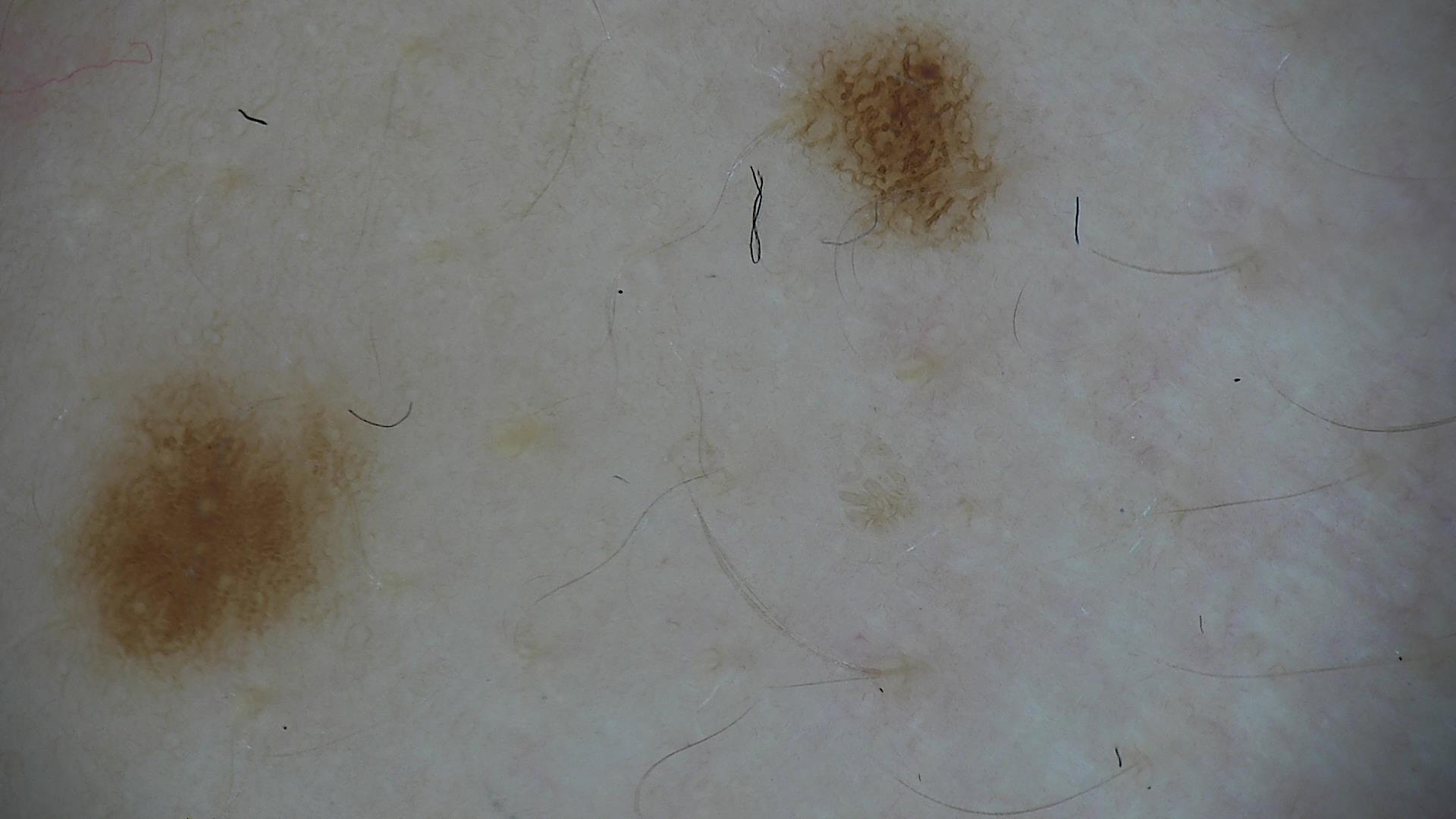image: dermatoscopy | assessment: dysplastic junctional nevus (expert consensus).